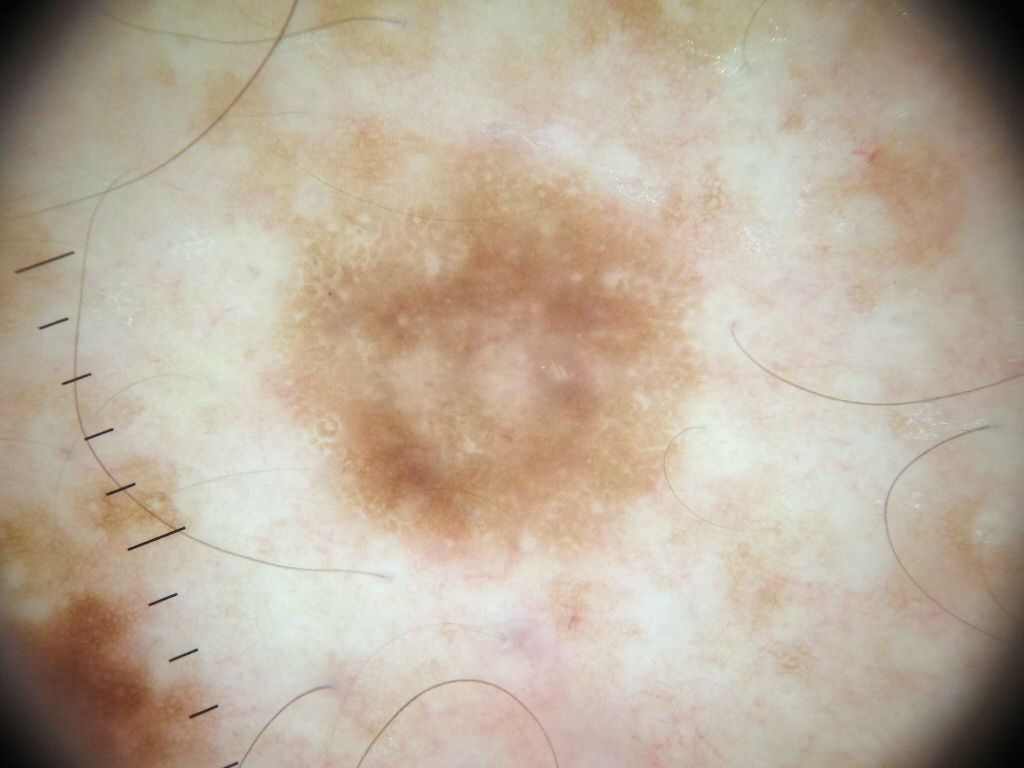Q: What is the imaging modality?
A: dermatoscopic image of a skin lesion
Q: What are the patient's age and sex?
A: male, aged approximately 40
Q: What does dermoscopy show?
A: negative network and pigment network; absent: milia-like cysts, globules, and streaks
Q: How large is the lesion within the image?
A: ~27% of the field
Q: Where is the lesion located?
A: x1=210, y1=86, x2=745, y2=591
Q: What did the assessment conclude?
A: a melanocytic nevus, a benign lesion